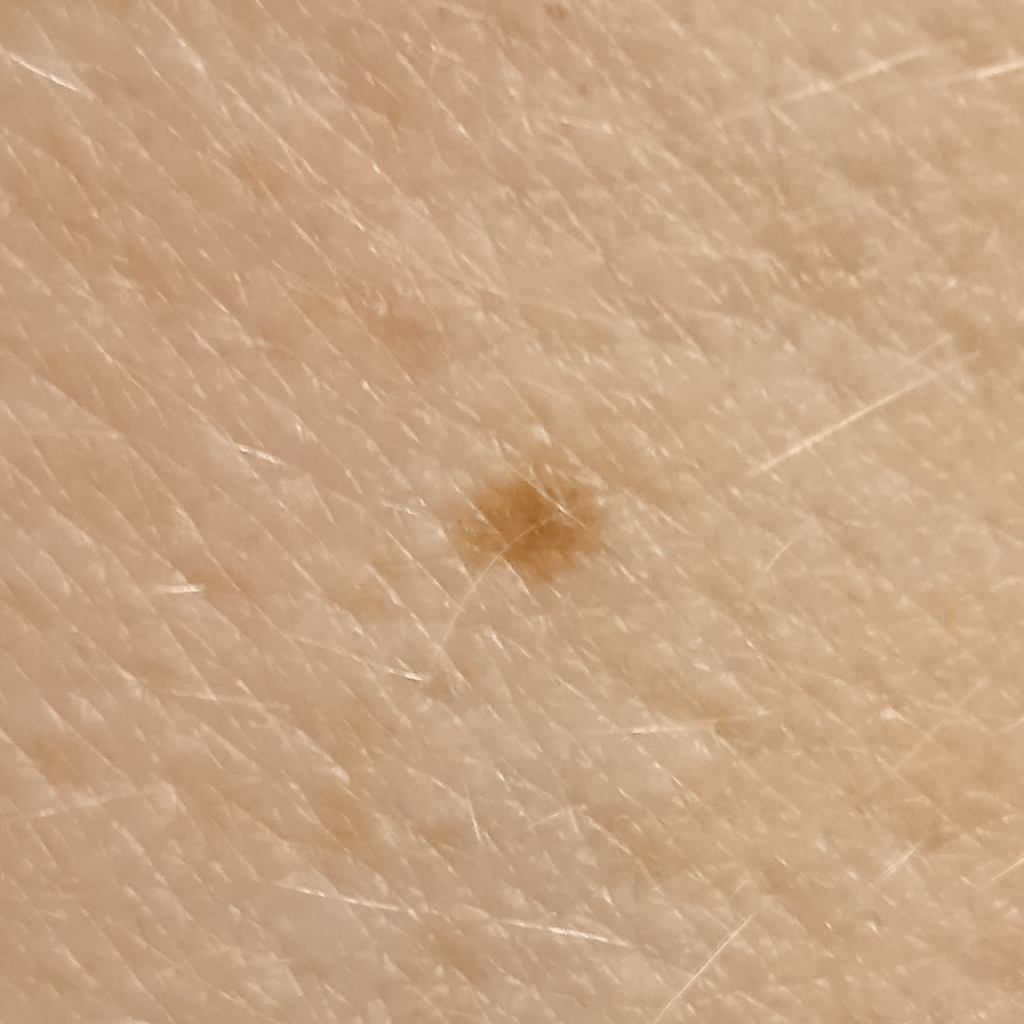Collected as part of a research study, without a referral diagnosis. The patient reports no personal history of cancer. The patient says their skin reddens painfully with sun exposure. A clinical close-up of a skin lesion. A female subject 50 years of age. A moderate number of moles by the patient's own estimate. Located on an arm. The lesion is about 2 mm across. The consensus diagnosis for this lesion was a melanocytic nevus.